A dermoscopic close-up of a skin lesion: 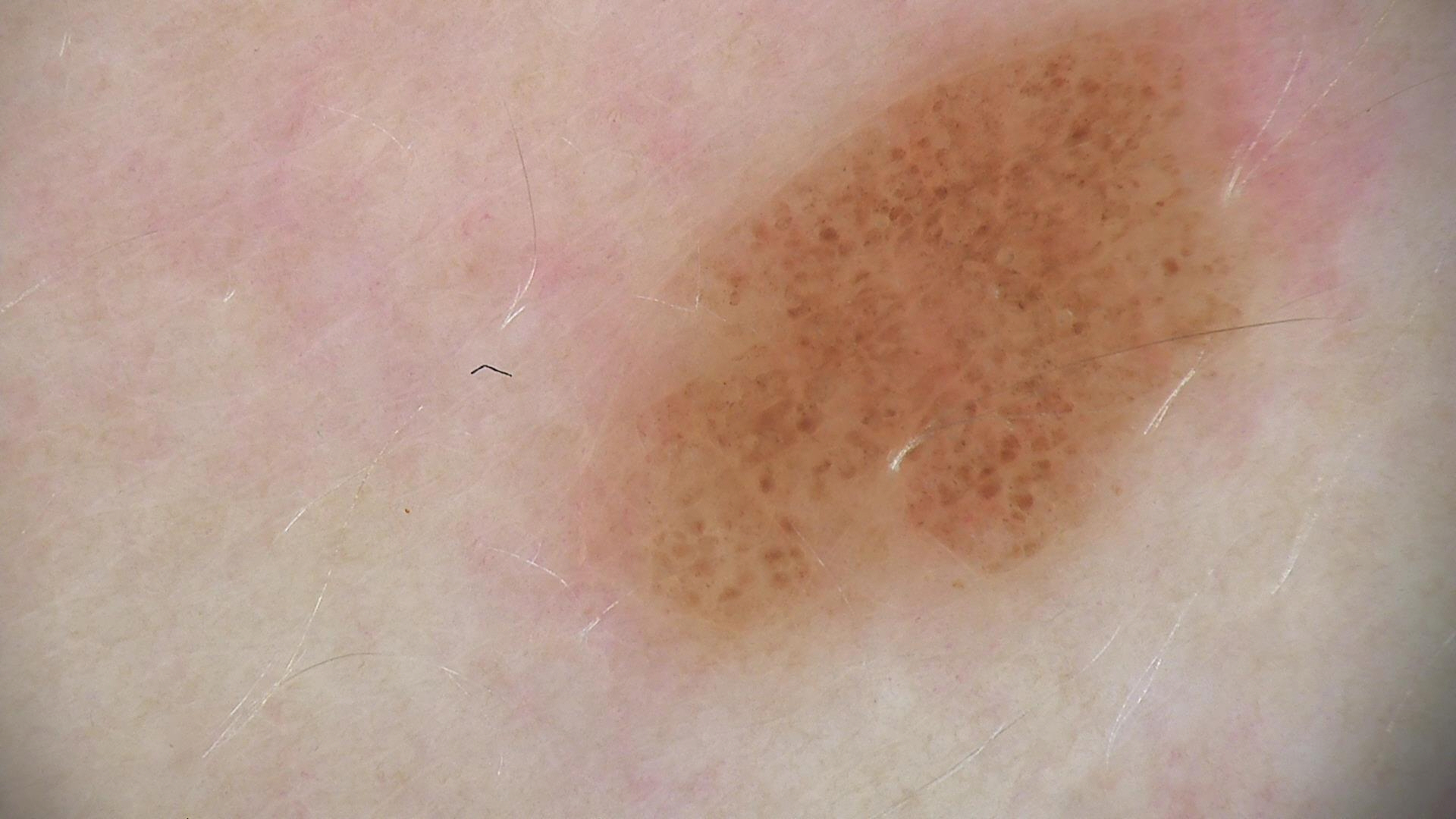Case:
* diagnosis — junctional nevus (expert consensus)